A dermatoscopic image of a skin lesion.
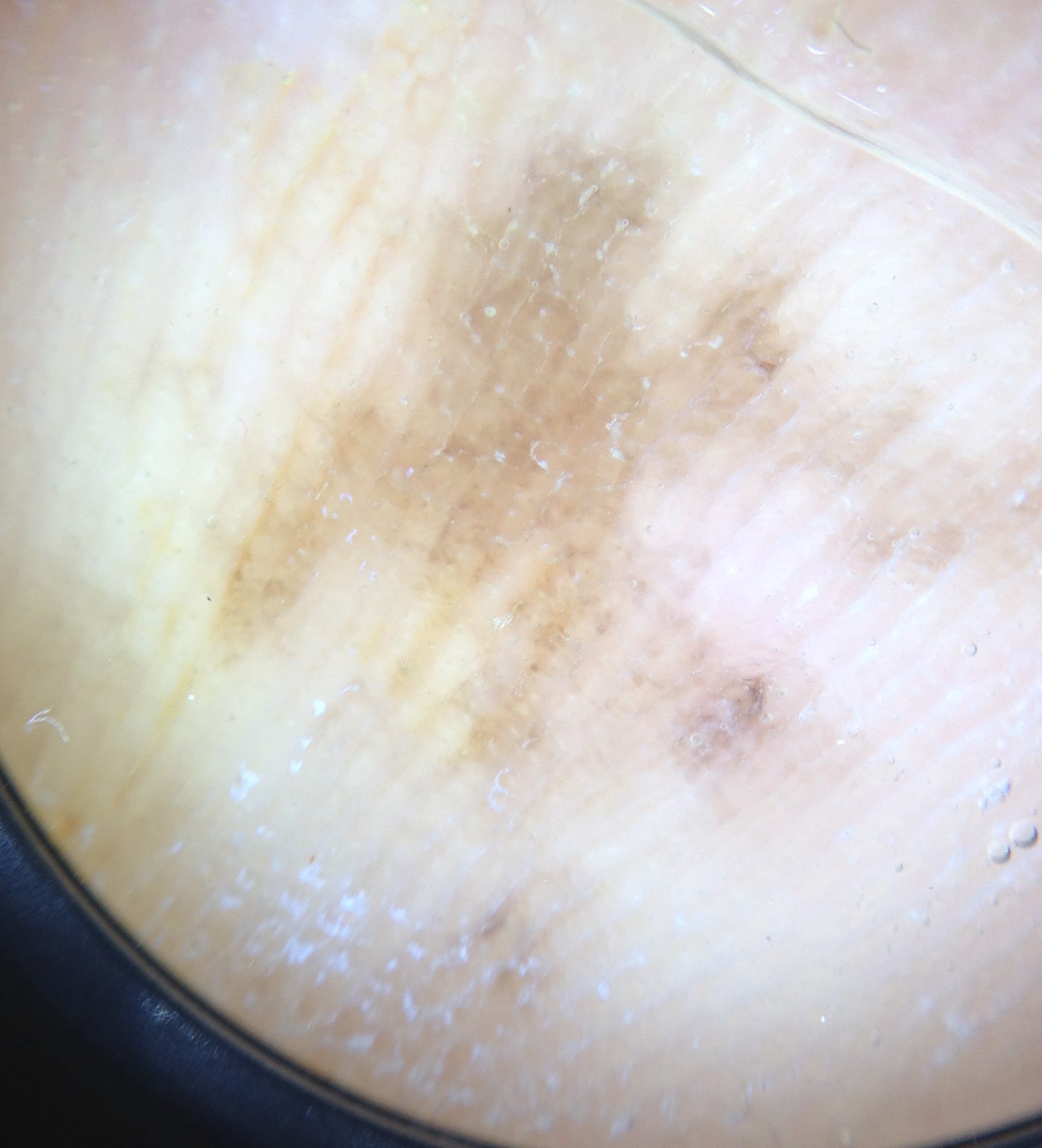Histopathology confirmed an acral lentiginous melanoma.